A smartphone photograph of a skin lesion. A patient 39 years old — 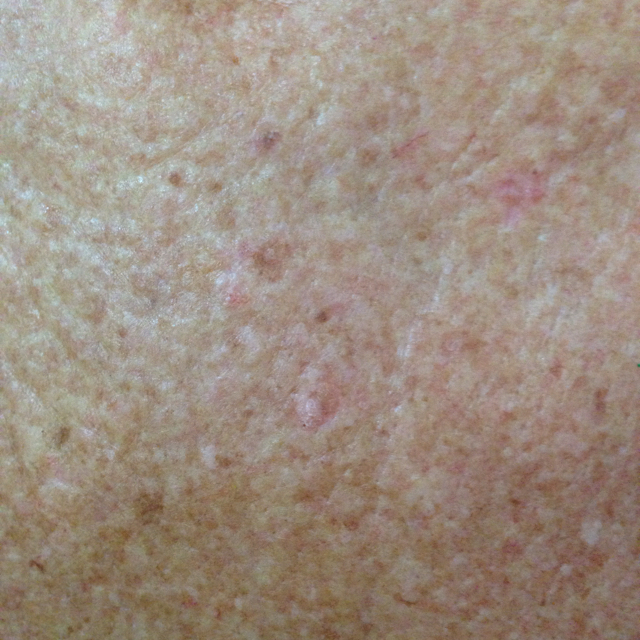Findings:
• patient-reported symptoms · itching
• impression · actinic keratosis (clinical consensus)